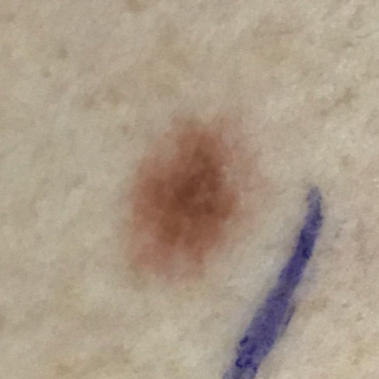{"image": "smartphone clinical photo", "risk_factors": {"positive": ["prior cancer (patient or family)"]}, "lesion_location": "the back", "lesion_size": {"diameter_1_mm": 7.0, "diameter_2_mm": 4.0}, "symptoms": {"present": ["itching"]}, "diagnosis": {"name": "nevus", "code": "NEV", "malignancy": "benign", "confirmation": "histopathology"}}